A dermoscopic view of a skin lesion:
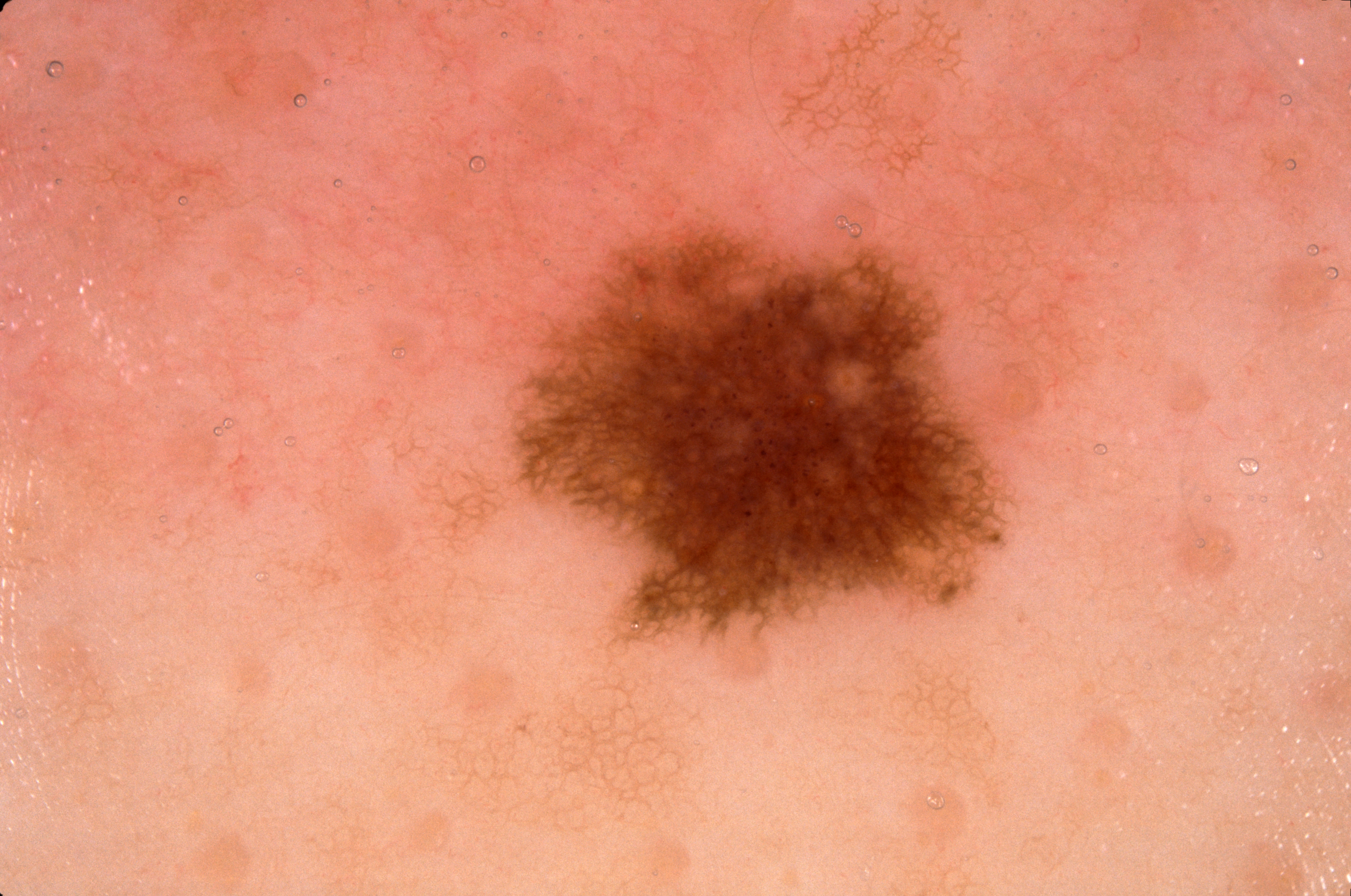On dermoscopy, the lesion shows pigment network. The lesion is bounded by <bbox>509, 210, 1014, 643</bbox>. The lesion was assessed as a melanocytic nevus, a benign lesion.